Close-up view · located on the back of the hand:
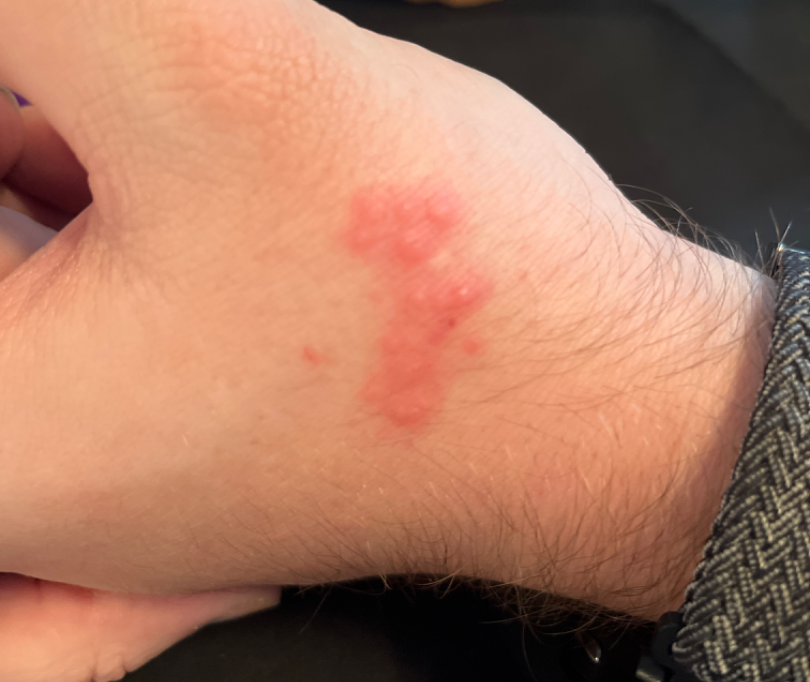Findings:
• self-categorized as: a rash
• constitutional symptoms: none reported
• lesion texture: raised or bumpy and fluid-filled
• present for: about one day
• symptoms: itching and bothersome appearance
• differential: Herpes Simplex (favored)